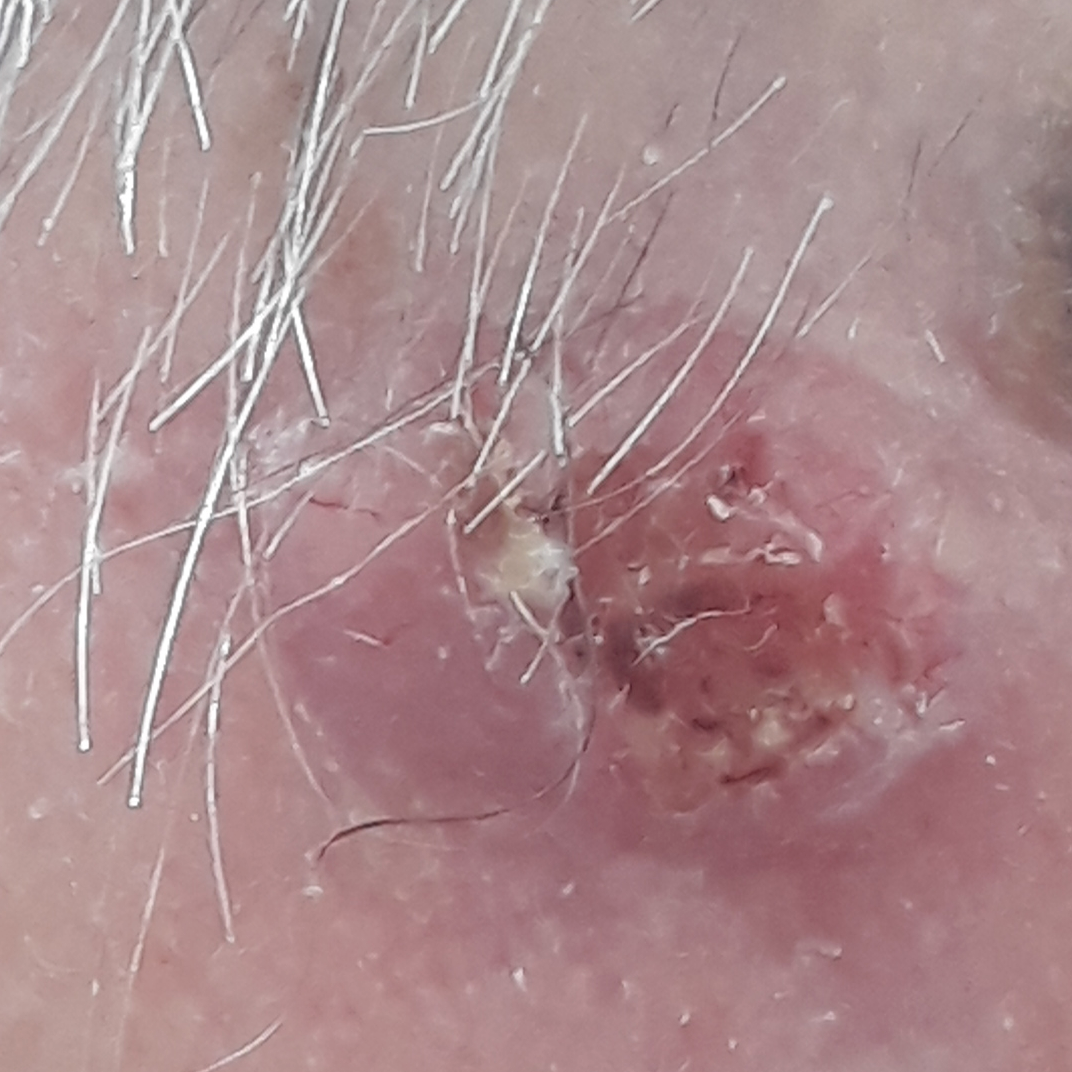| feature | finding |
|---|---|
| FST | II |
| patient | male, 79 years old |
| imaging | smartphone clinical photo |
| body site | the face |
| lesion size | 17 × 12 mm |
| symptoms | itching, growth, elevation / no change in appearance |
| pathology | basal cell carcinoma (biopsy-proven) |